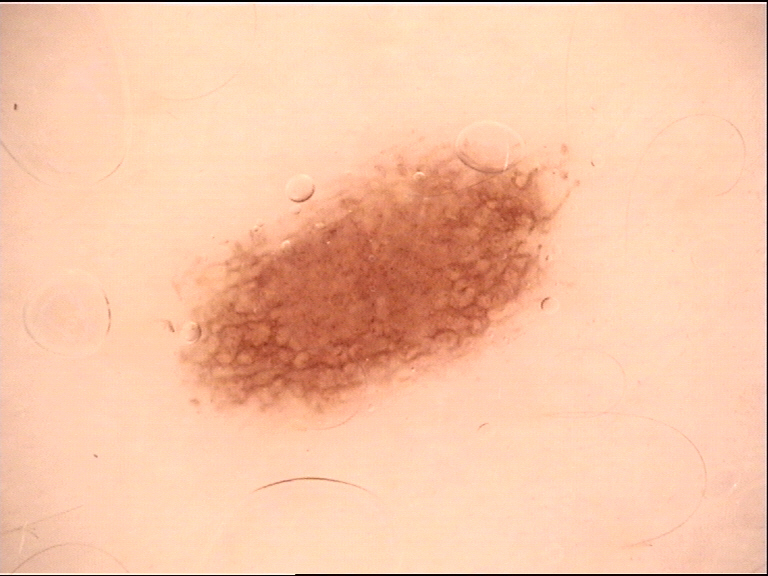Consistent with a dysplastic junctional nevus.